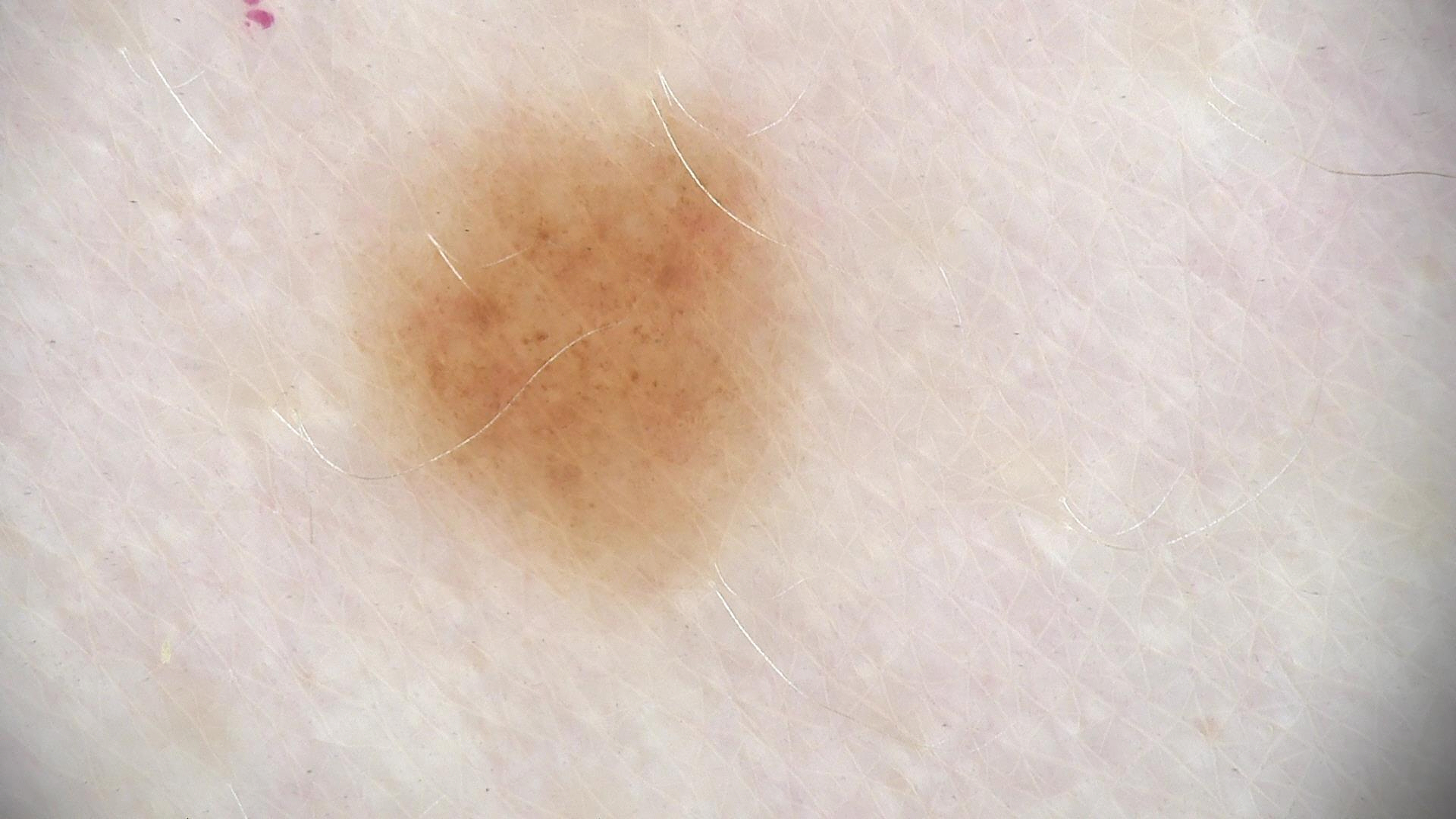Summary:
A dermoscopic photograph of a skin lesion.
Conclusion:
Consistent with a dysplastic junctional nevus.